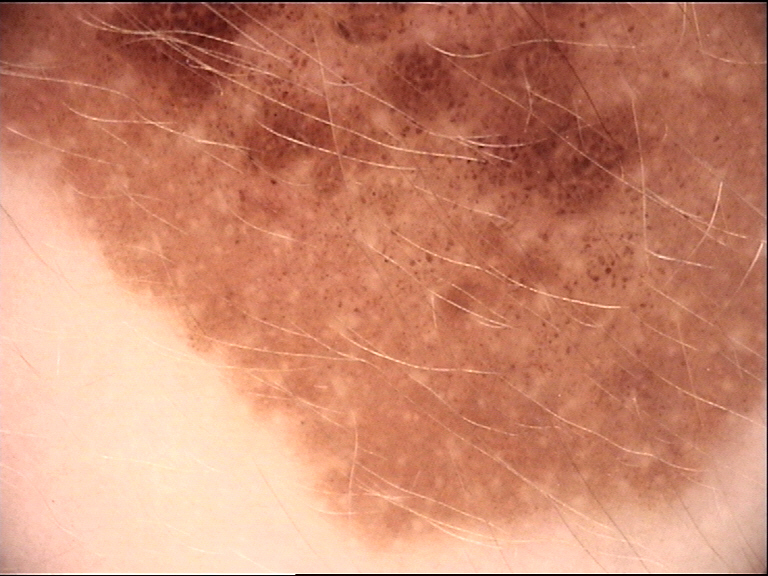lesion type = banal, label = congenital junctional nevus (expert consensus).